The lesion involves the top or side of the foot and leg · a close-up photograph.
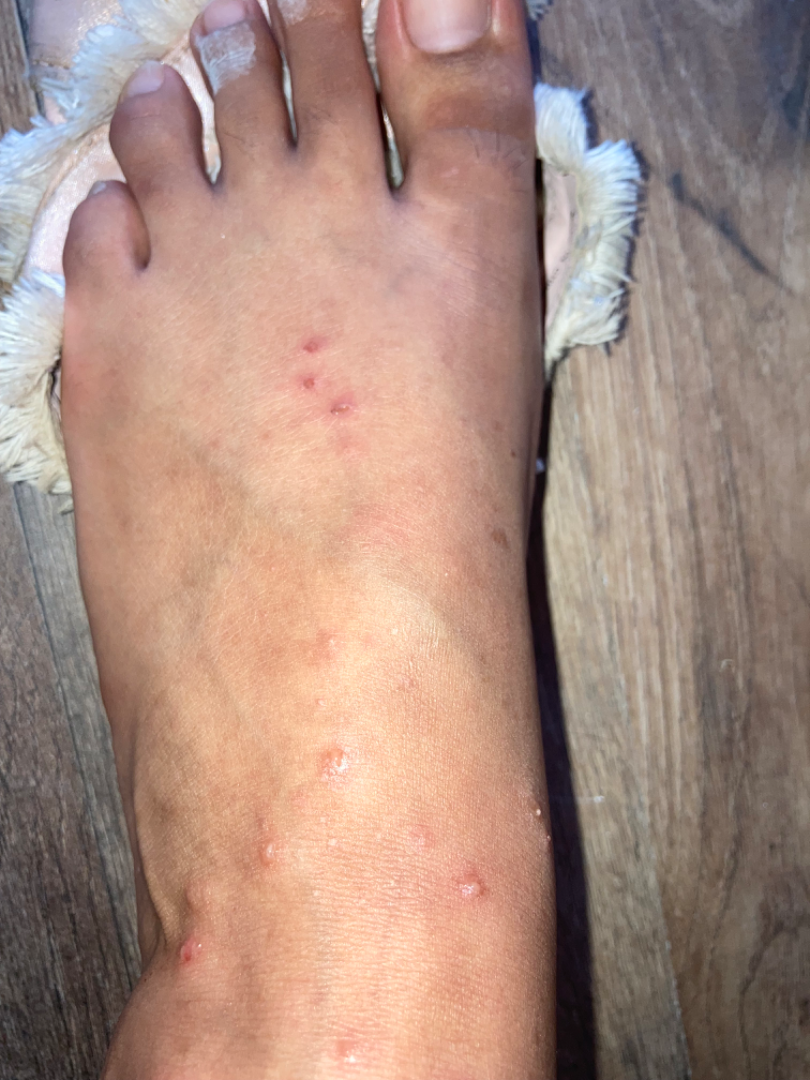Notes:
– differential diagnosis — most consistent with Insect Bite; an alternative is Scabies; possibly Allergic Contact Dermatitis